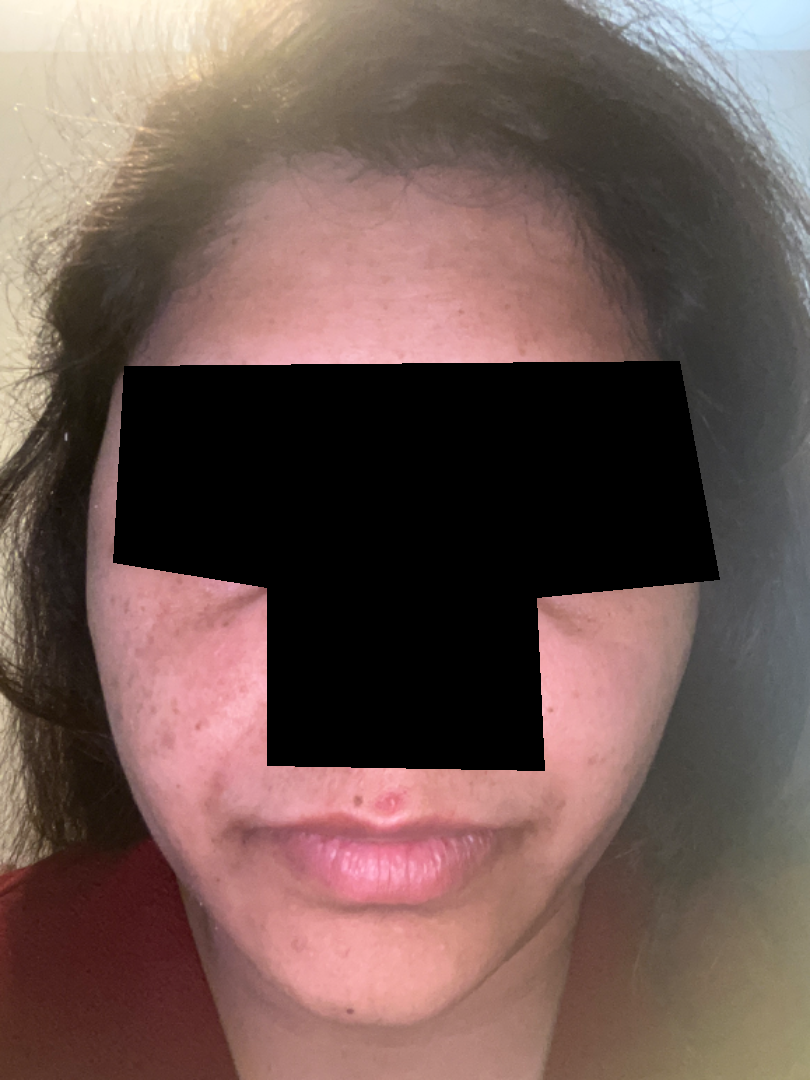Background: The condition has been present for more than one year. The photo was captured at an angle. The patient indicates the lesion is raised or bumpy and rough or flaky. Reported lesion symptoms include bothersome appearance and darkening. The contributor is a female aged 30–39. Self-categorized by the patient as acne. Findings: The reviewing dermatologists' impression was: most consistent with Acne; the differential also includes Perioral Dermatitis.